The affected area is the leg, the photo was captured at an angle, Fitzpatrick skin type II; non-clinician graders estimated a MST of 4, texture is reported as raised or bumpy, the condition has been present for about one day, the patient considered this skin that appeared healthy to them — 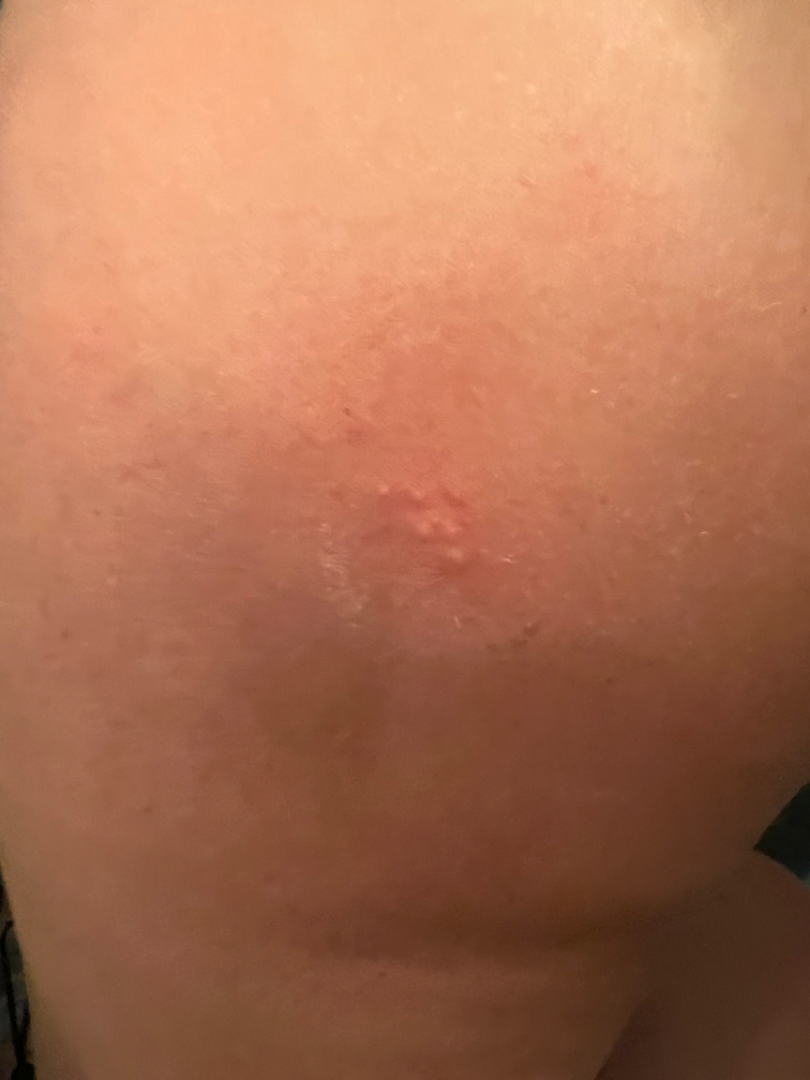The differential, in no particular order, includes Acne, Molluscum Contagiosum and Herpes Simplex.